A subject 67 years of age:
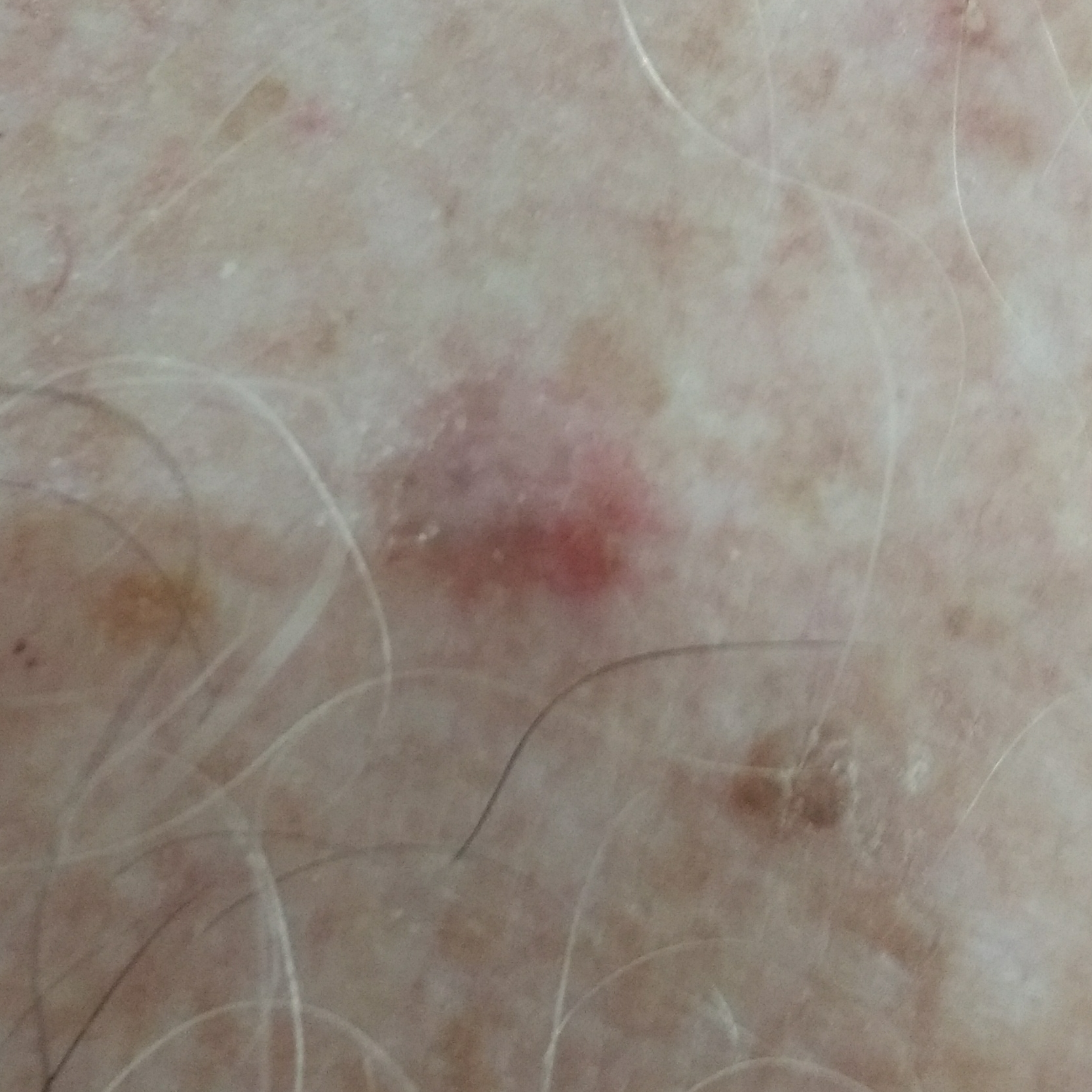Q: What does the patient describe?
A: itching
Q: What is the diagnosis?
A: actinic keratosis (clinical consensus)